Close-up view:
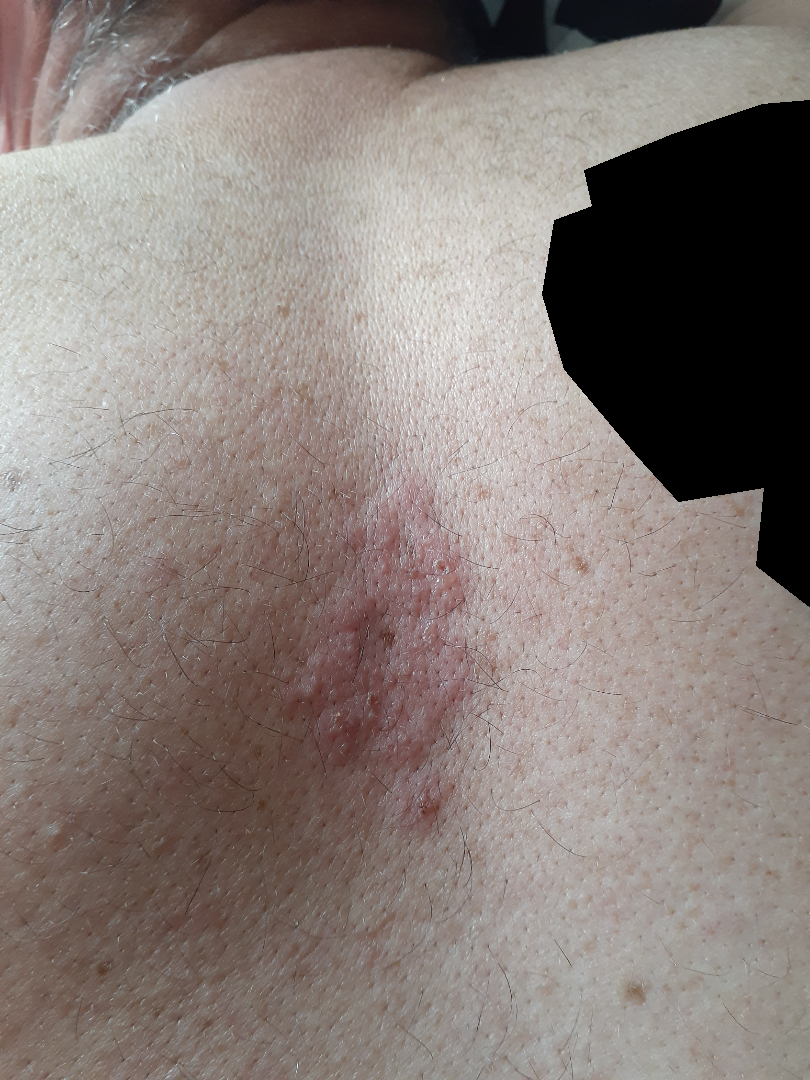{
  "differential": {
    "tied_lead": [
      "Eczema",
      "Allergic Contact Dermatitis"
    ],
    "unlikely": [
      "Herpes Simplex"
    ]
  }
}